This image was taken at a distance — 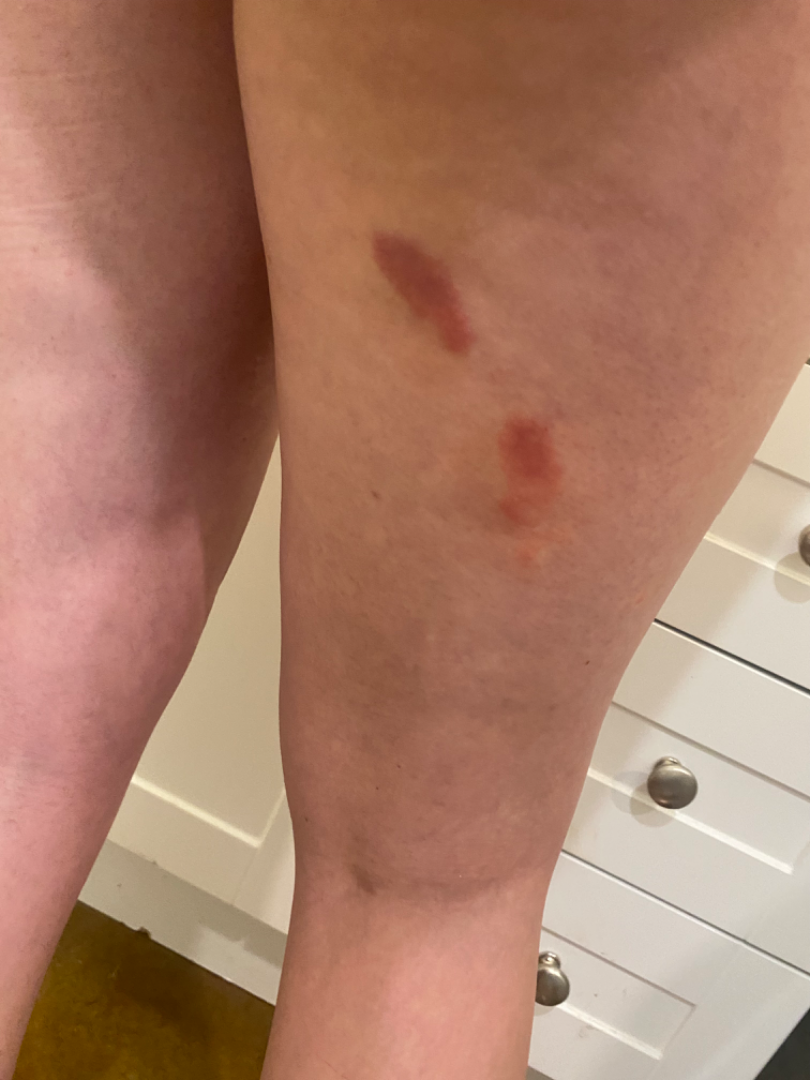  assessment: could not be assessed